The condition has been present for more than one year · the patient also reports mouth sores · the lesion is described as raised or bumpy, fluid-filled, rough or flaky and flat · an image taken at an angle · the lesion is associated with itching, bleeding, pain, darkening, enlargement and bothersome appearance · the lesion involves the arm, front of the torso, top or side of the foot, back of the torso, back of the hand, head or neck and leg · non-clinician graders estimated Monk skin tone scale 3 — 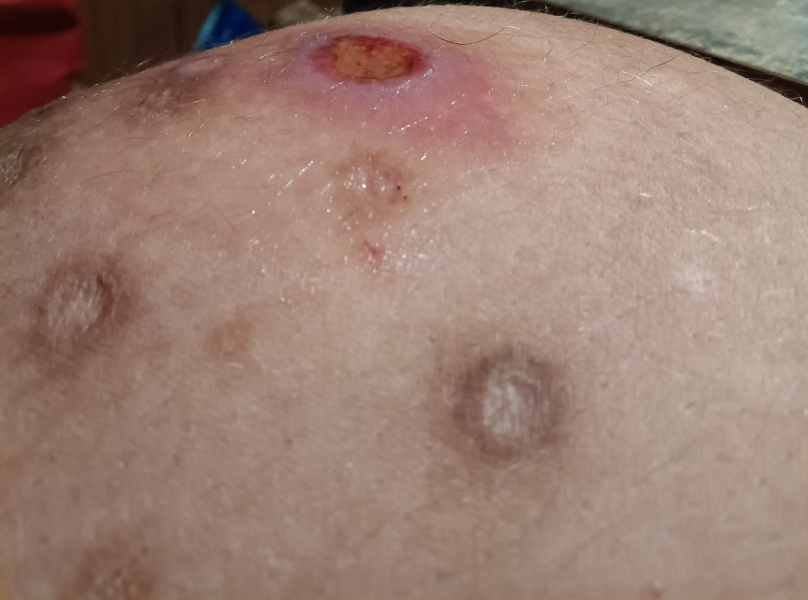diagnostic considerations: most consistent with Skin lesion in drug addict; also raised was Ecthyma; less probable is Acute ulcer of skin.